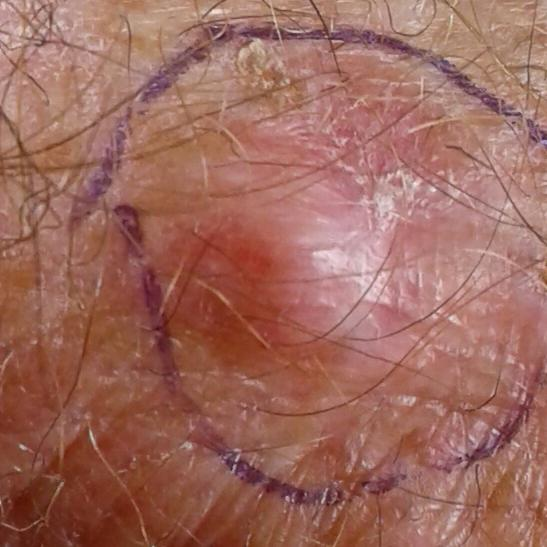Recorded as Fitzpatrick phototype II. History notes alcohol use, prior malignancy (patient or family), and prior skin cancer (patient or family). A clinical photograph of a skin lesion. A male patient 58 years of age. Located on a hand. The lesion measures approximately 13 × 10 mm. The patient describes that the lesion itches and is elevated, but has not changed. Histopathologically confirmed as a basal cell carcinoma.